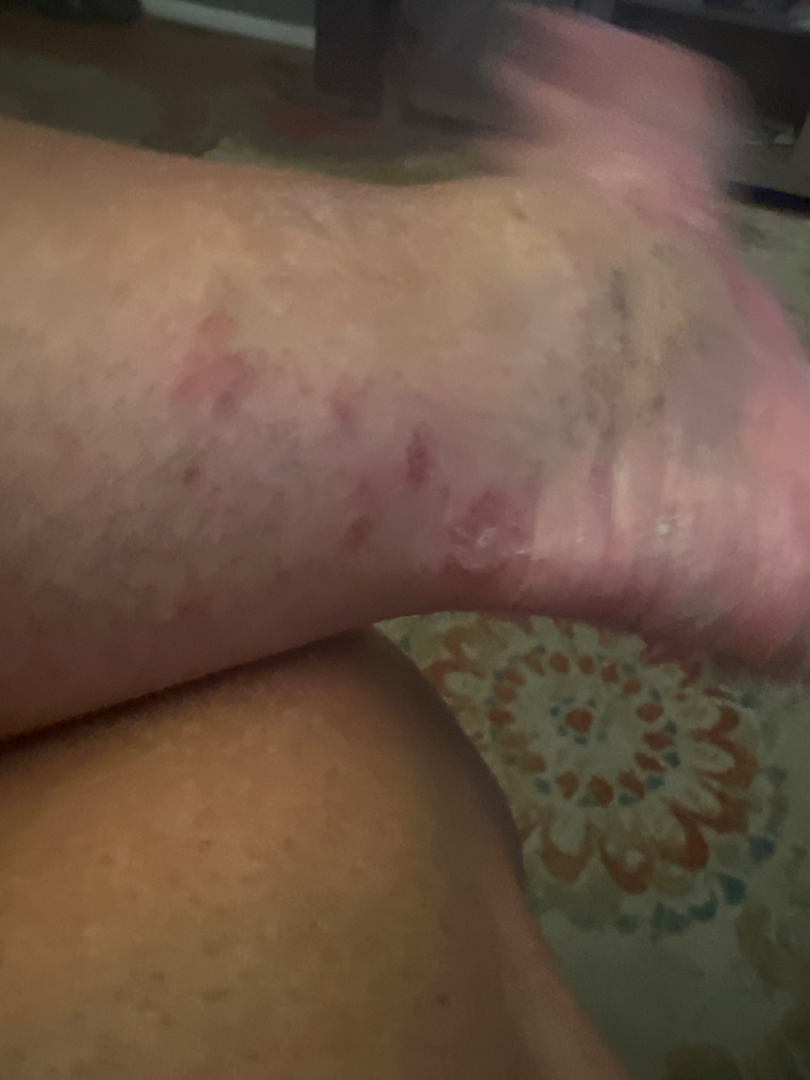The skin findings could not be characterized from the image.